The affected area is the arm. Female patient, age 18–29. Close-up view:
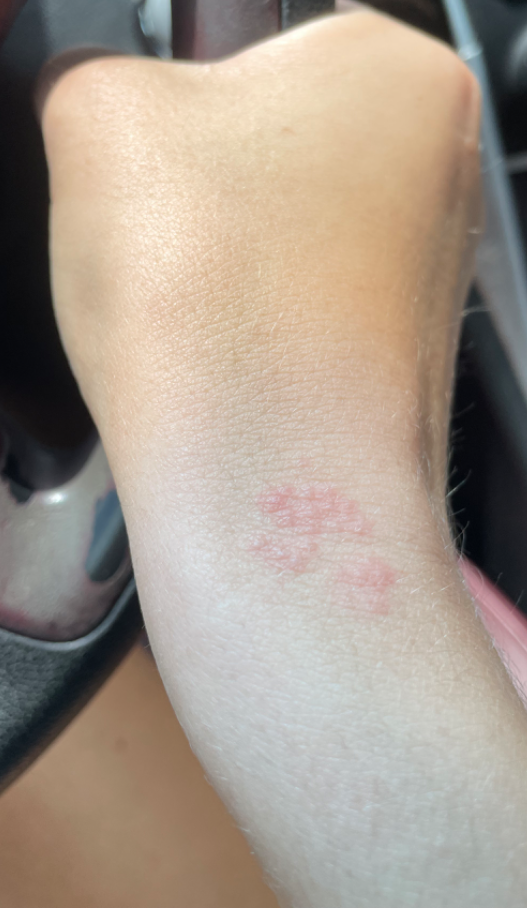Impression:
The reviewing dermatologist's impression was: Allergic Contact Dermatitis (weight 0.54); Eczema (weight 0.23); Irritant Contact Dermatitis (weight 0.23).